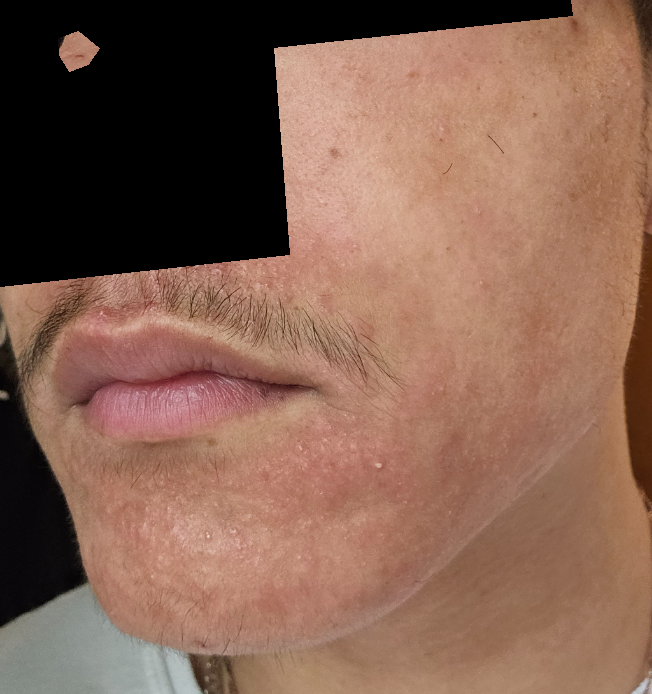| field | value |
|---|---|
| assessment | ungradable on photographic review |
| skin tone | Fitzpatrick II; human graders estimated Monk skin tone scale 2 |
| framing | at an angle |